A dermatoscopic image of a skin lesion: 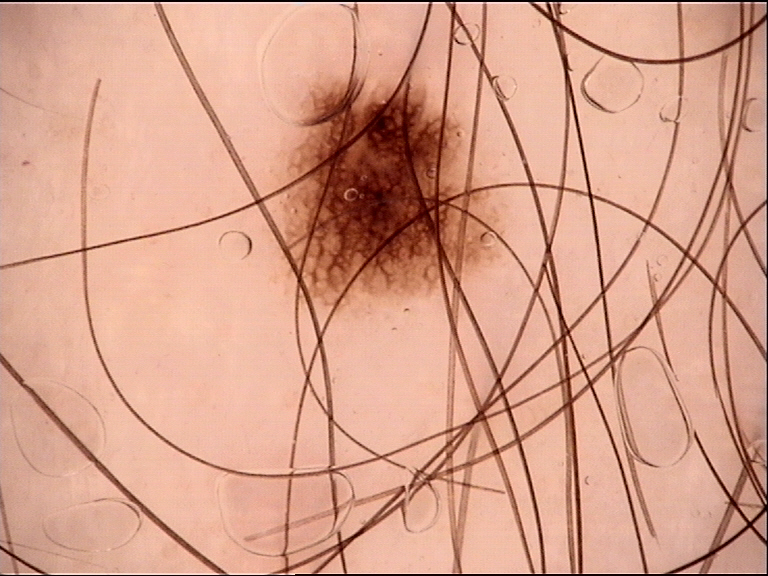Impression: Labeled as a benign lesion — a dysplastic junctional nevus.